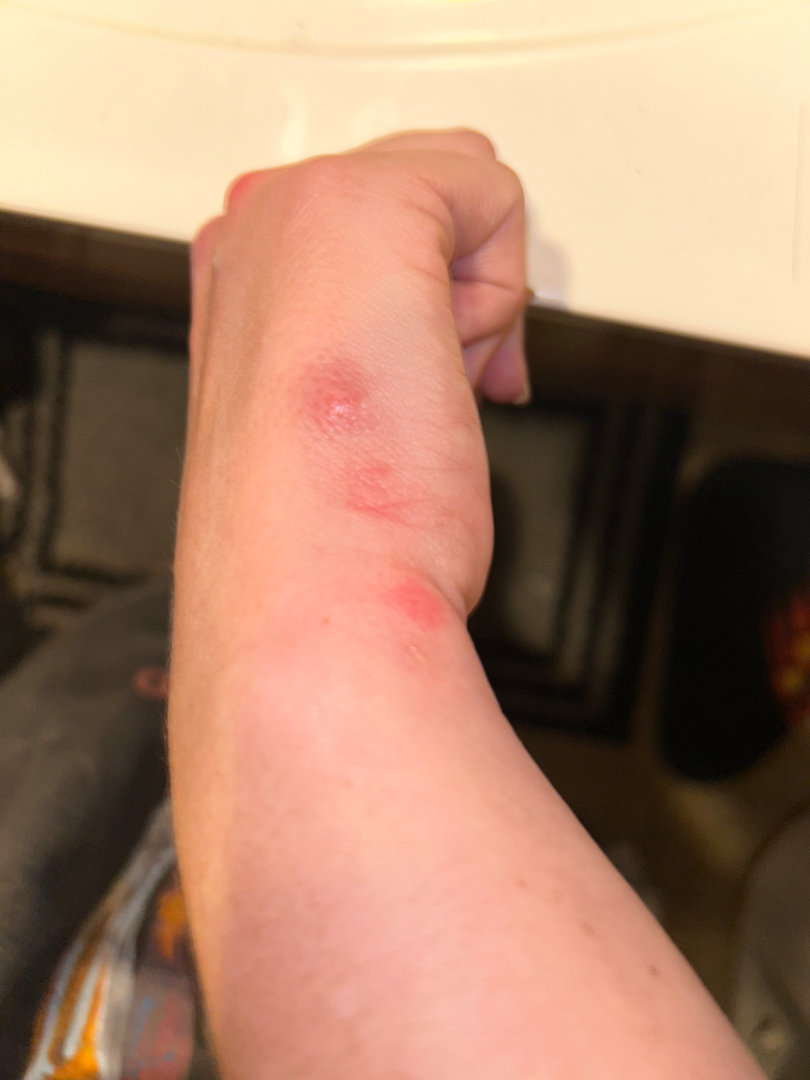The reviewer was unable to grade this case for skin condition. A close-up photograph. Female patient, age 30–39.